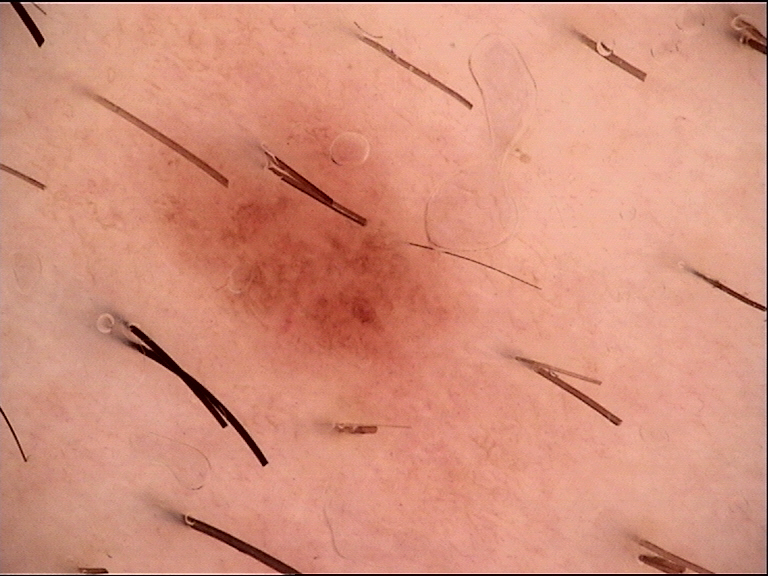Q: What is the imaging modality?
A: dermoscopy
Q: What was the diagnostic impression?
A: dysplastic junctional nevus (expert consensus)